This image was taken at an angle. Fitzpatrick III; lay reviewers estimated 2 on the Monk skin tone scale:
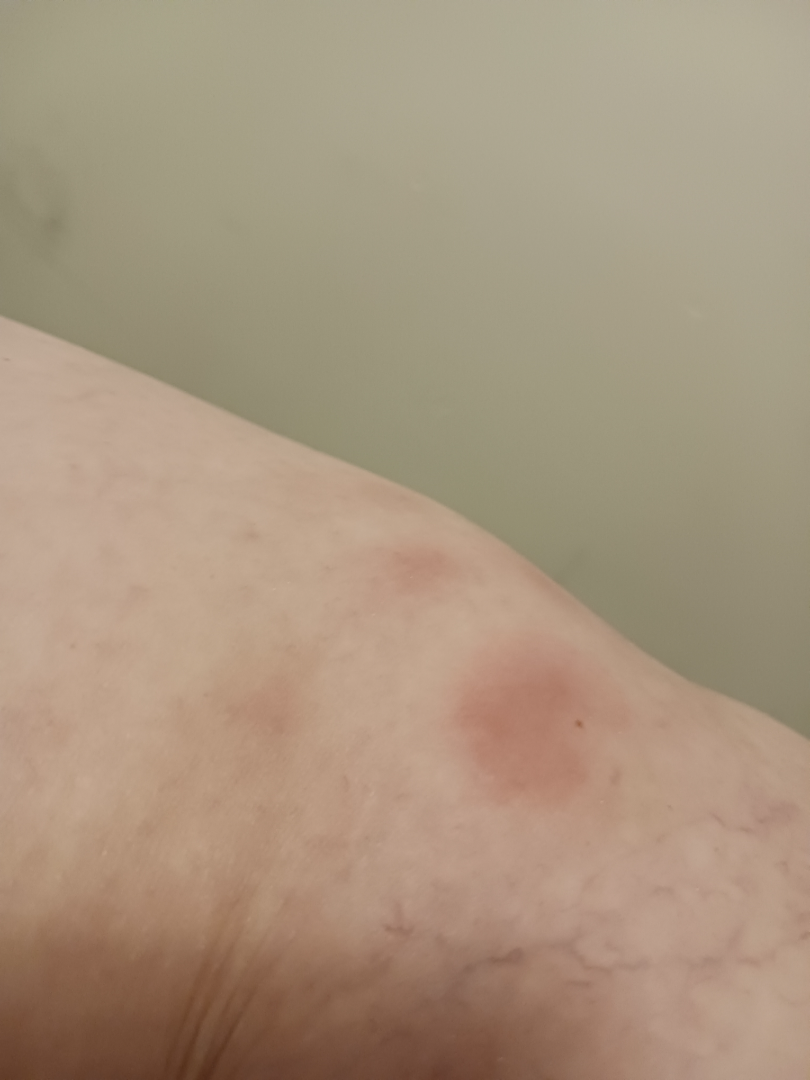Review: Reviewed remotely by one dermatologist: the leading impression is Erythema nodosum; also consider Panniculitis, NOS; less probable is Insect Bite.